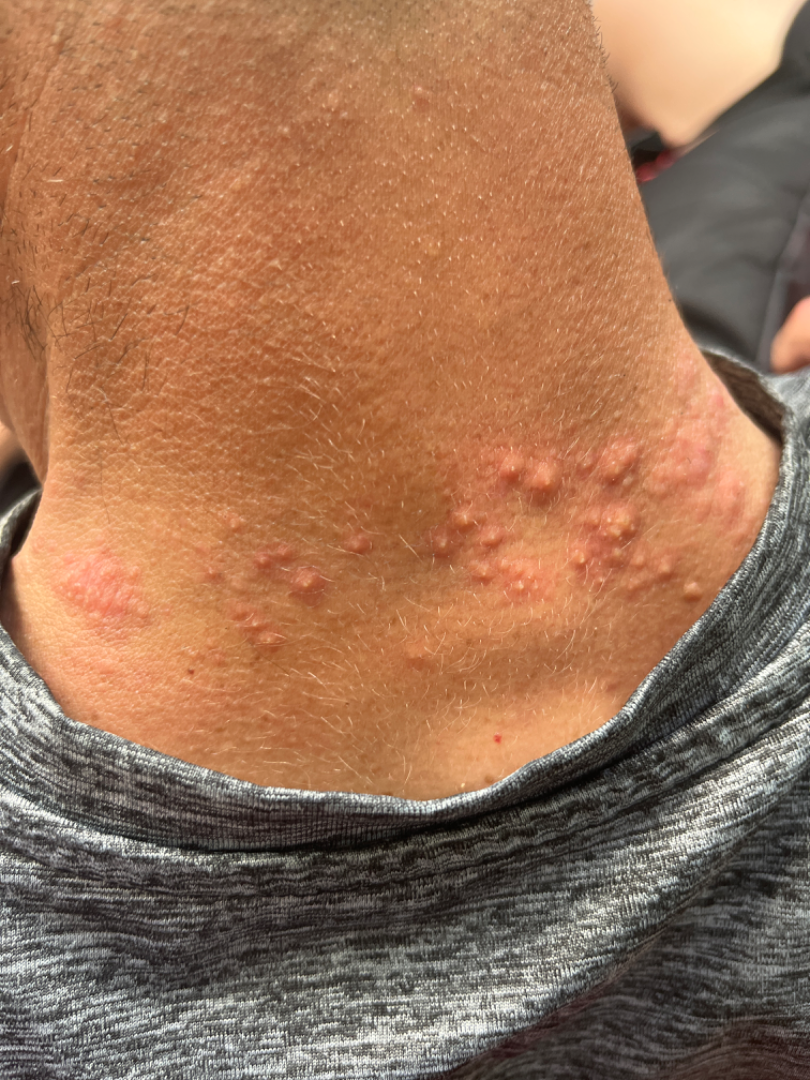Patient information:
The head or neck is involved. This is a close-up image. No constitutional symptoms were reported. Symptoms reported: itching. The patient considered this a rash.
Review:
Single-reviewer assessment: consistent with Folliculitis.